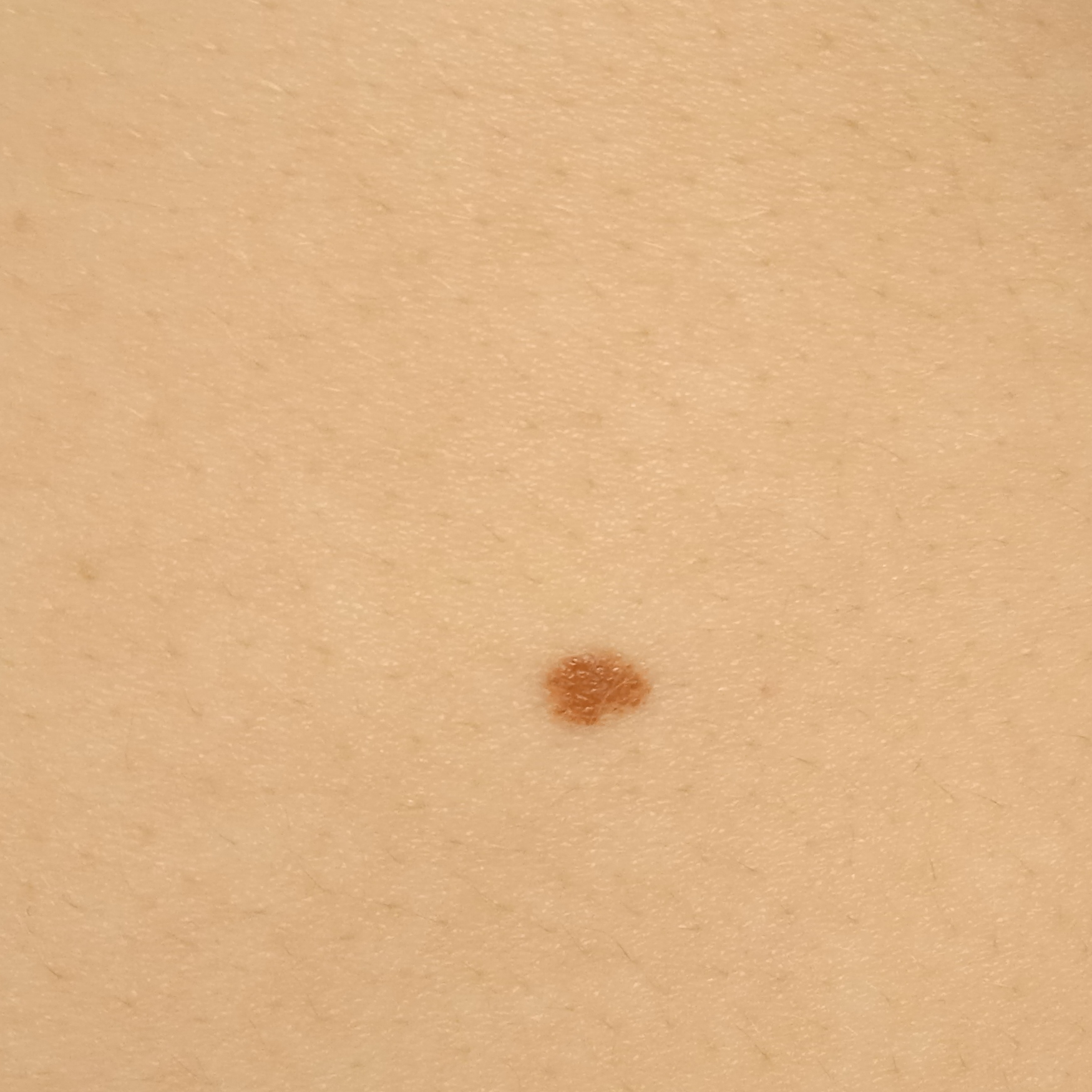| field | value |
|---|---|
| image type | clinical photo |
| referral context | research study (no referral diagnosis) |
| subject | female, 20 years old |
| site | the torso |
| size | 5.1 mm |
| diagnostic label | melanocytic nevus (dermatologist consensus) |